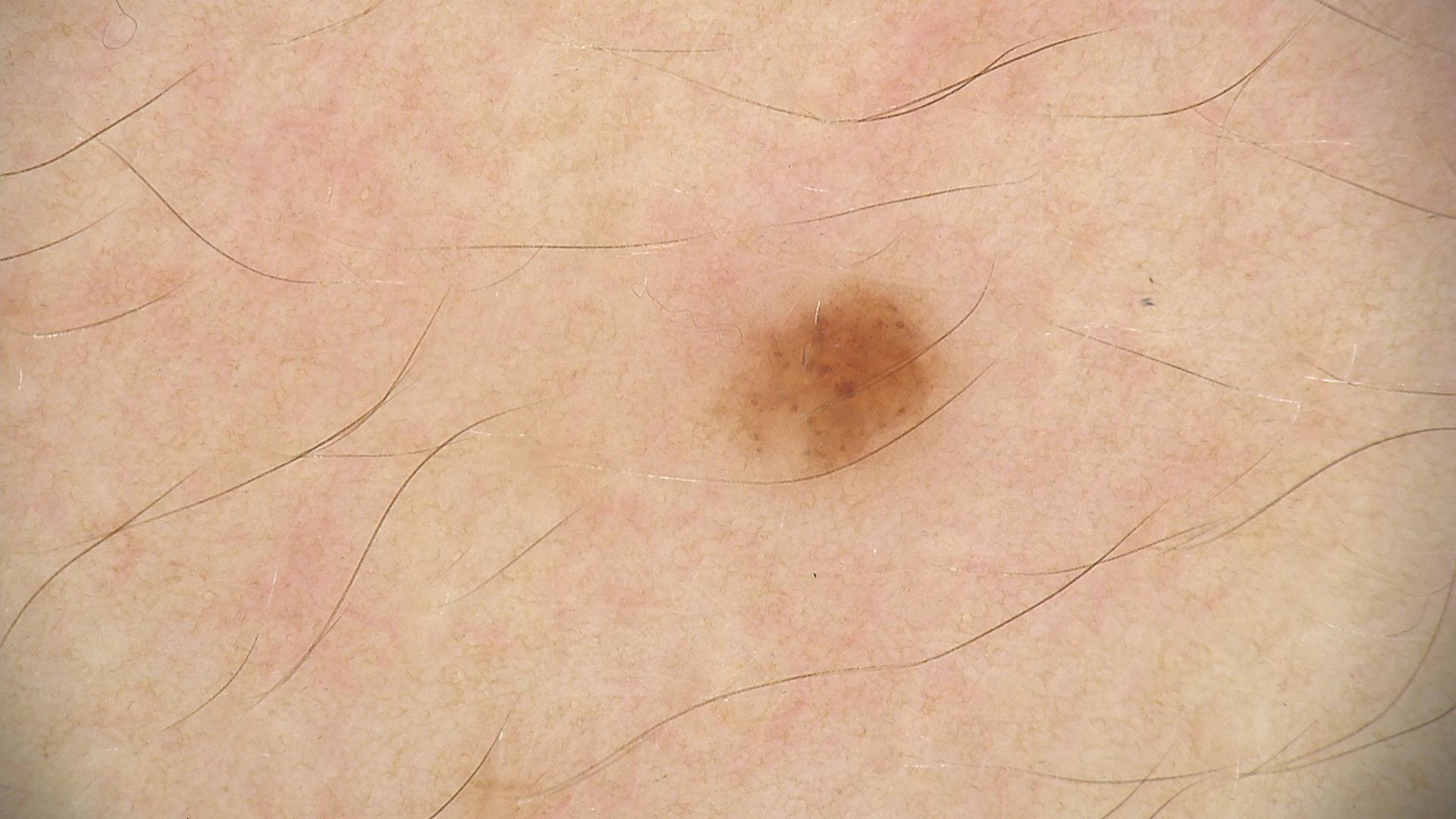The diagnosis was a dysplastic junctional nevus.